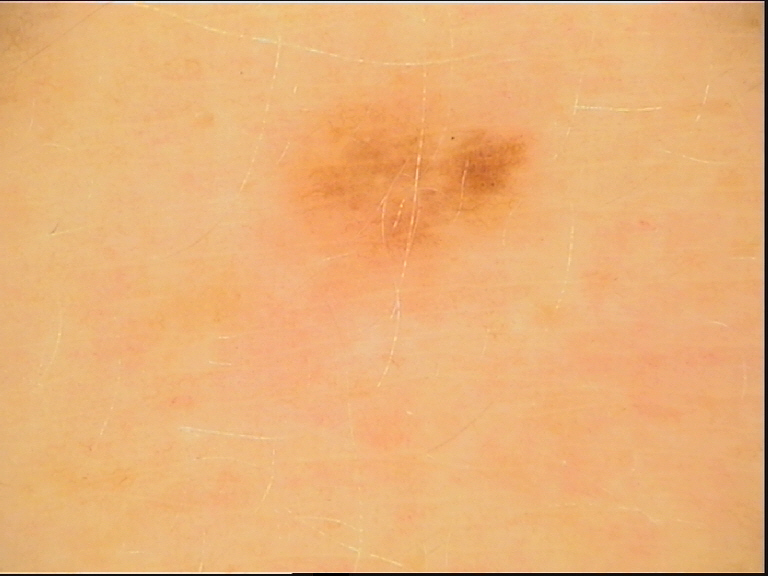label — dysplastic junctional nevus (expert consensus)